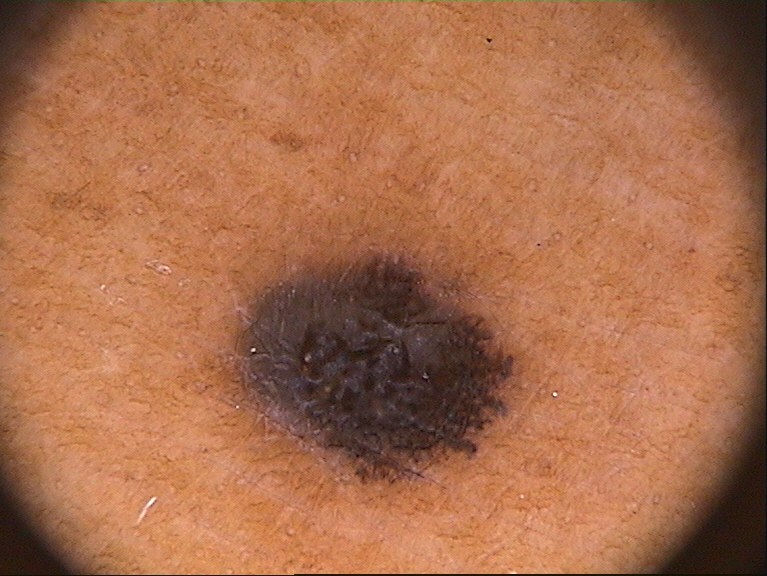image type = dermatoscopic image of a skin lesion; subject = male, approximately 50 years of age; size = ~11% of the field; lesion location = left=230, top=248, right=513, bottom=480; absent dermoscopic features = negative network, globules, streaks, pigment network, and milia-like cysts; assessment = a melanoma, a malignant skin lesion.